This is a dermoscopic photograph of a skin lesion — 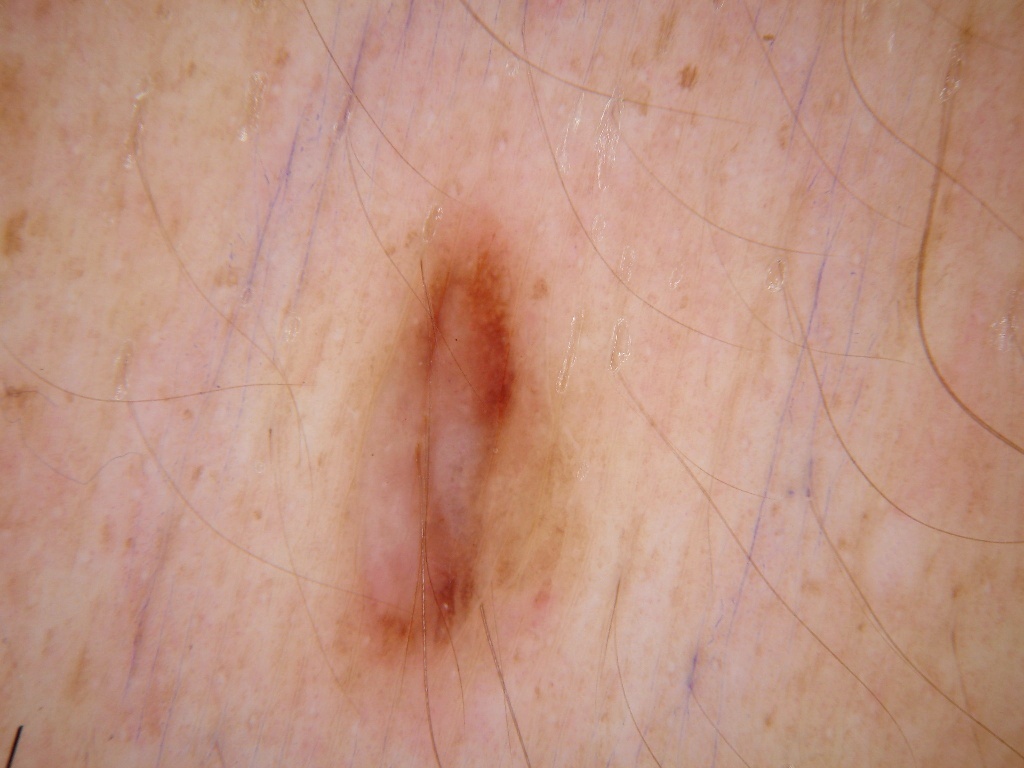  lesion_location:
    bbox_xyxy:
      - 319
      - 192
      - 591
      - 697
  diagnosis:
    name: melanocytic nevus
    malignancy: benign
    lineage: melanocytic
    provenance: clinical